The patient described the issue as a rash · male subject, age 18–29 · the leg, back of the torso and arm are involved · texture is reported as flat · the photograph was taken at an angle:
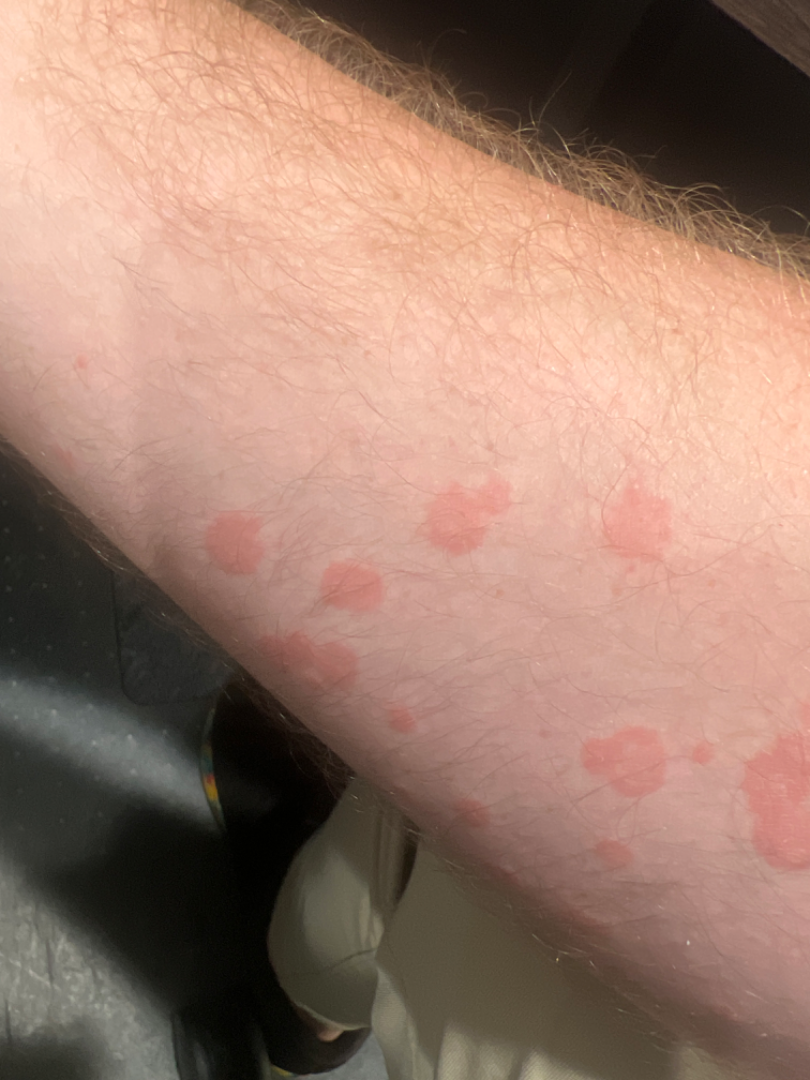assessment: not assessable.